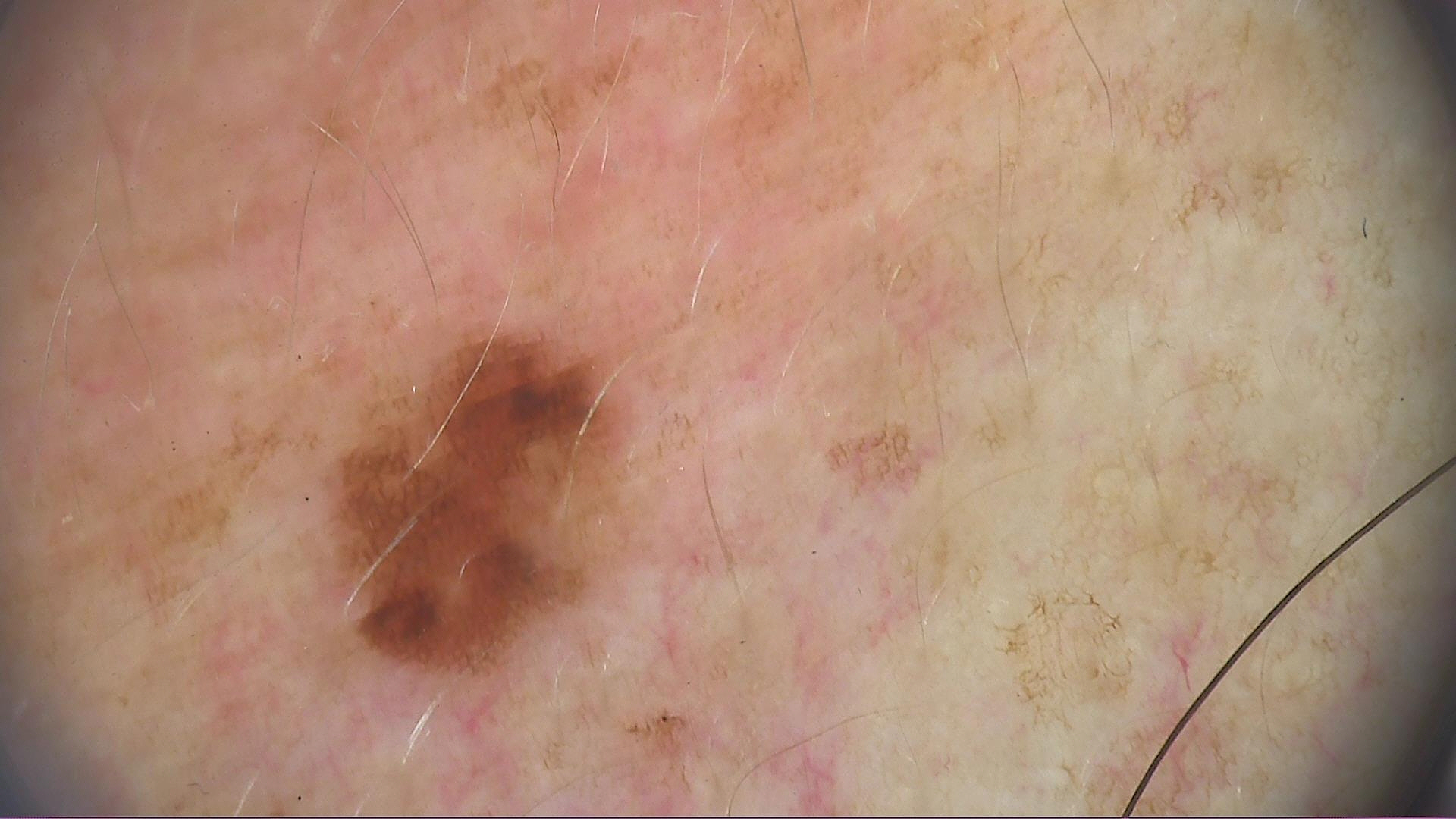Conclusion: Diagnosed as a dysplastic junctional nevus.